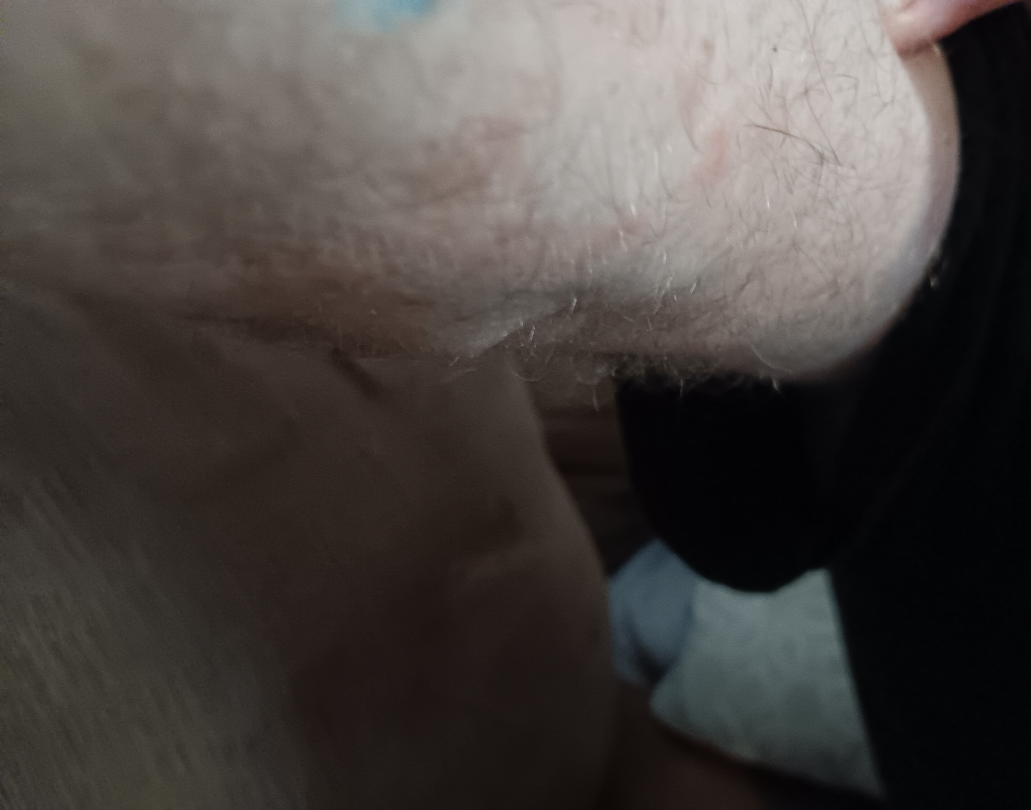assessment = ungradable on photographic review | image framing = close-up | site = arm.